A dermatoscopic image of a skin lesion; a female patient aged approximately 30:
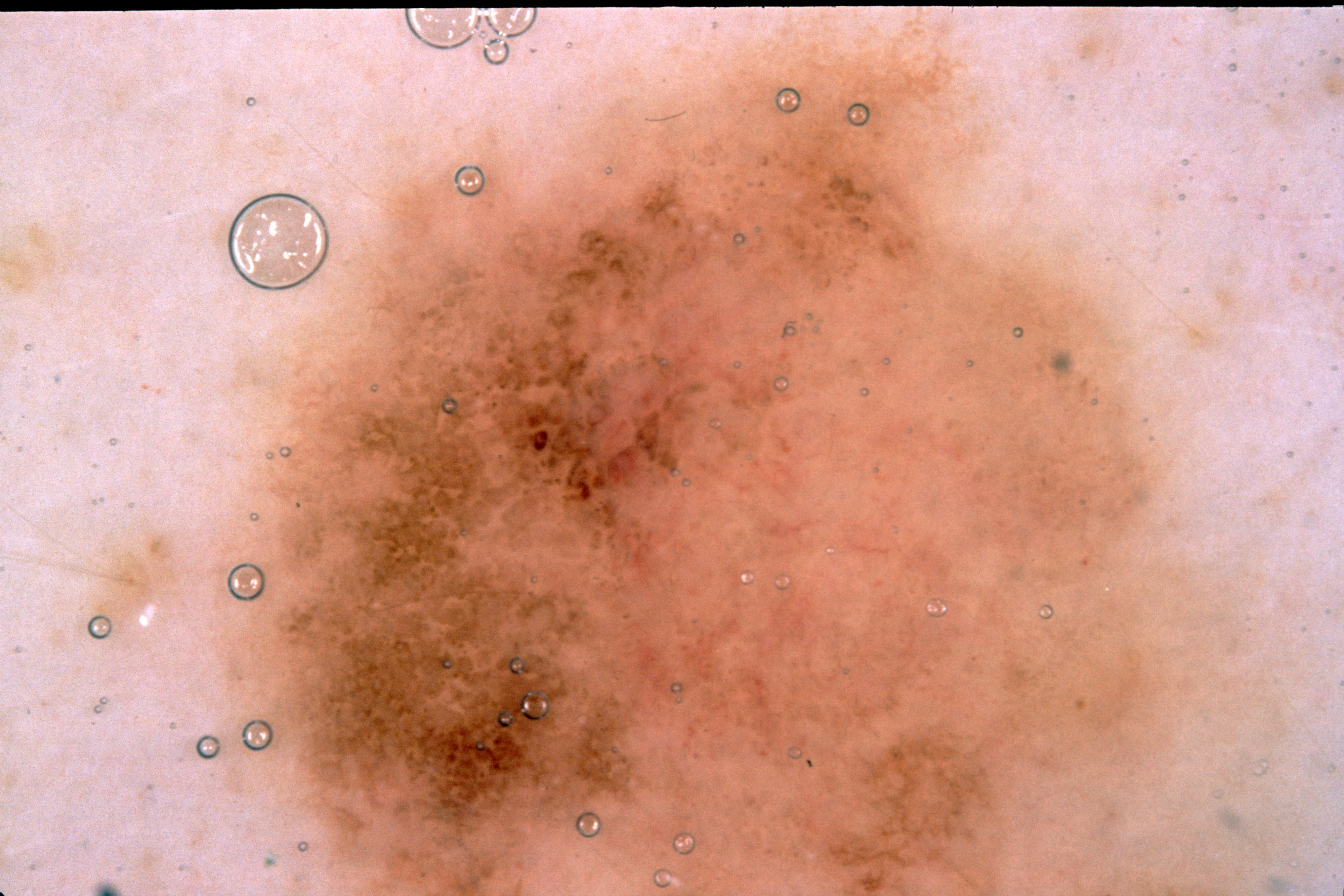Case summary:
• dermoscopic features · negative network; absent: streaks, milia-like cysts, and pigment network
• location · <box>206, 27, 1289, 895</box>
• diagnostic label · a melanocytic nevus